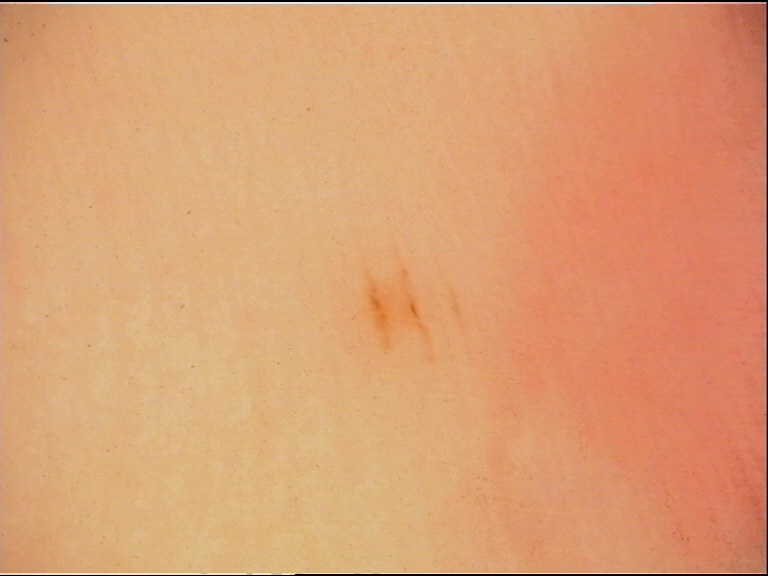Conclusion: Consistent with an acral junctional nevus.